The patient notes the condition has been present for one to four weeks; the patient notes the lesion is raised or bumpy; the patient considered this a rash; a close-up photograph; reported lesion symptoms include enlargement and itching; the affected area is the arm.
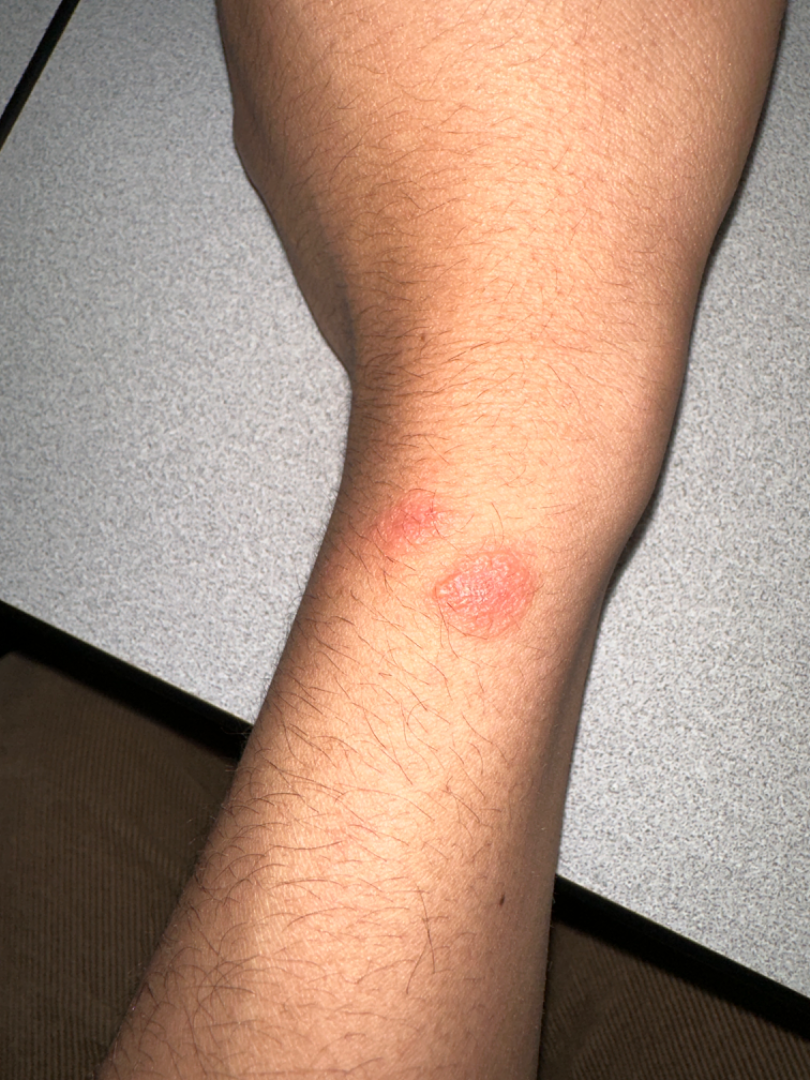Impression:
On remote dermatologist review, in keeping with Allergic Contact Dermatitis.